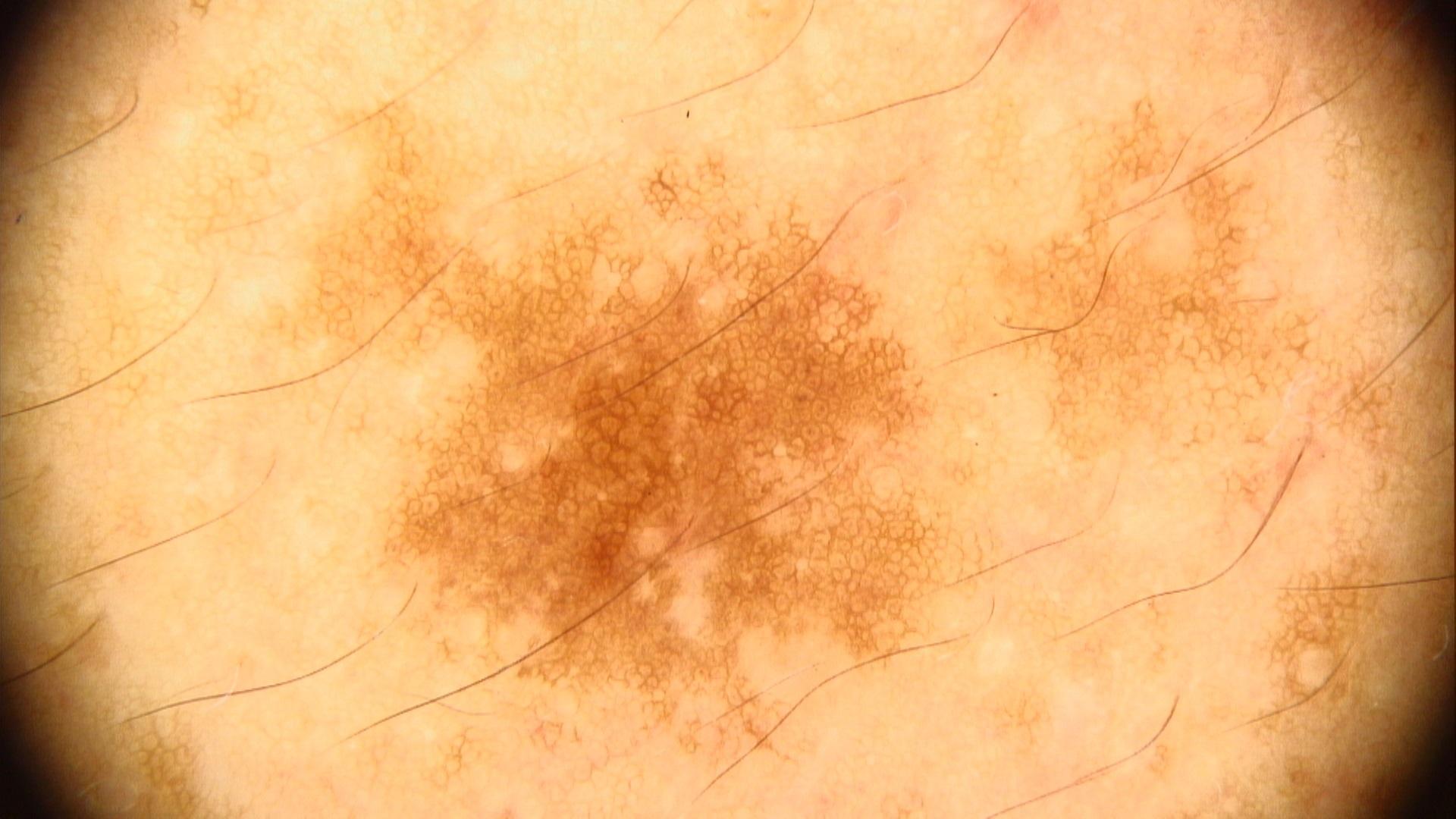{"patient": {"age_approx": 40, "sex": "male"}, "image": "contact-polarized dermoscopy", "diagnosis": {"name": "Nevus", "malignancy": "benign", "confirmation": "expert clinical impression", "lineage": "melanocytic"}}